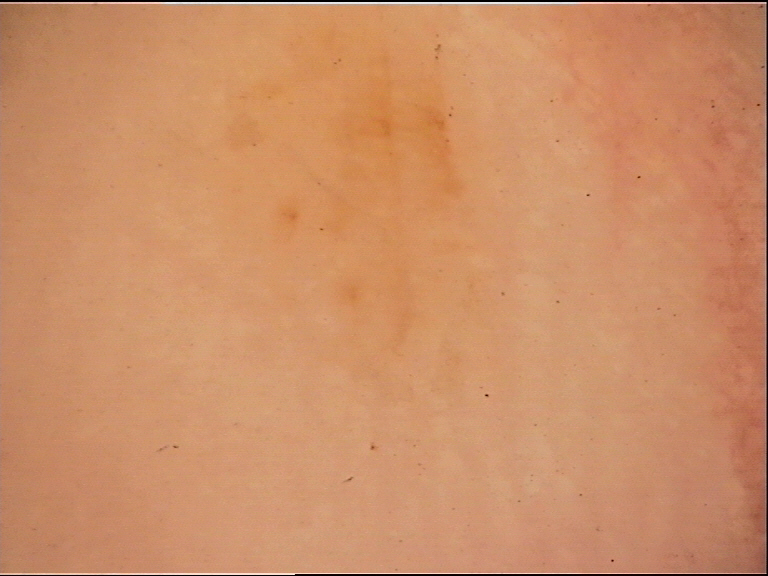A dermoscopy image of a single skin lesion.
This is a banal lesion.
Labeled as an acral junctional nevus.